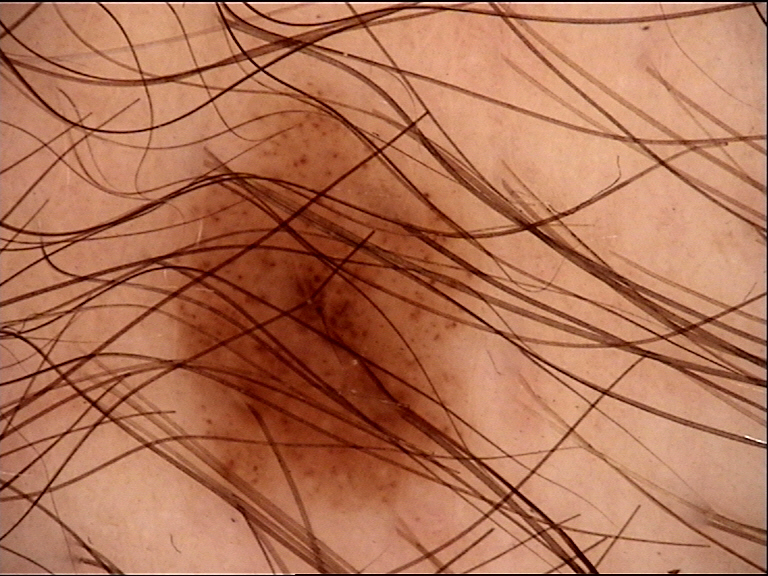Findings: A dermatoscopic image of a skin lesion. Impression: Classified as a benign lesion — a dysplastic junctional nevus.